The affected area is the leg, this image was taken at a distance, the patient is a female aged 50–59.
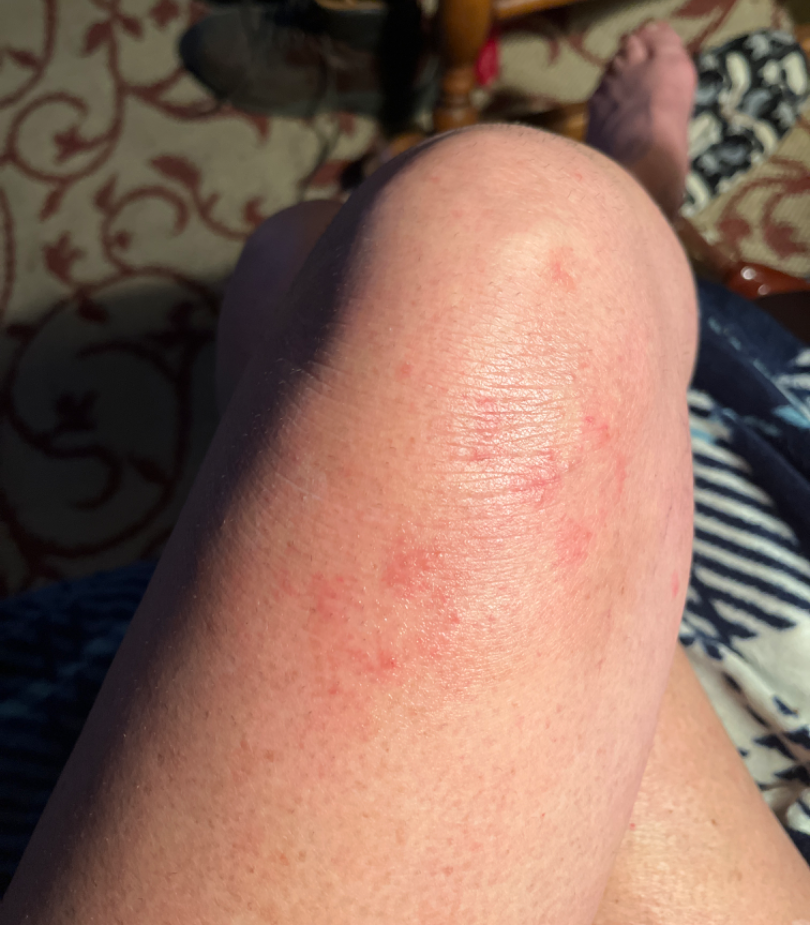The patient notes the lesion is raised or bumpy. Reported lesion symptoms include itching. Self-categorized by the patient as a rash. The patient notes the condition has been present for more than one year. Consistent with Eczema.